A dermoscopic view of a skin lesion — 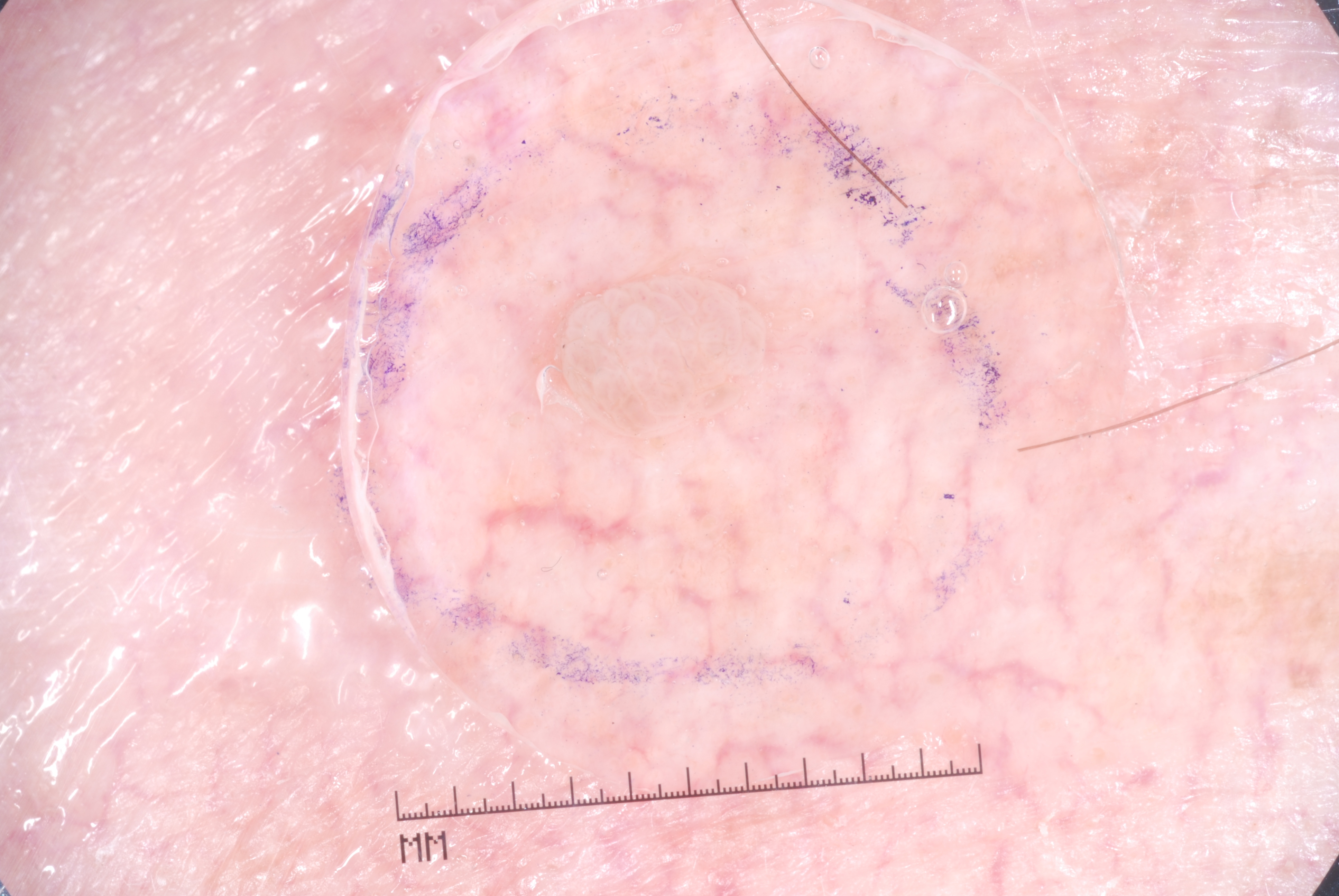<case>
<lesion_location>
  <bbox_xyxy>522, 239, 795, 459</bbox_xyxy>
</lesion_location>
<diagnosis>
  <name>seborrheic keratosis</name>
  <malignancy>benign</malignancy>
  <lineage>keratinocytic</lineage>
  <provenance>clinical</provenance>
</diagnosis>
</case>